A dermoscopy image of a single skin lesion:
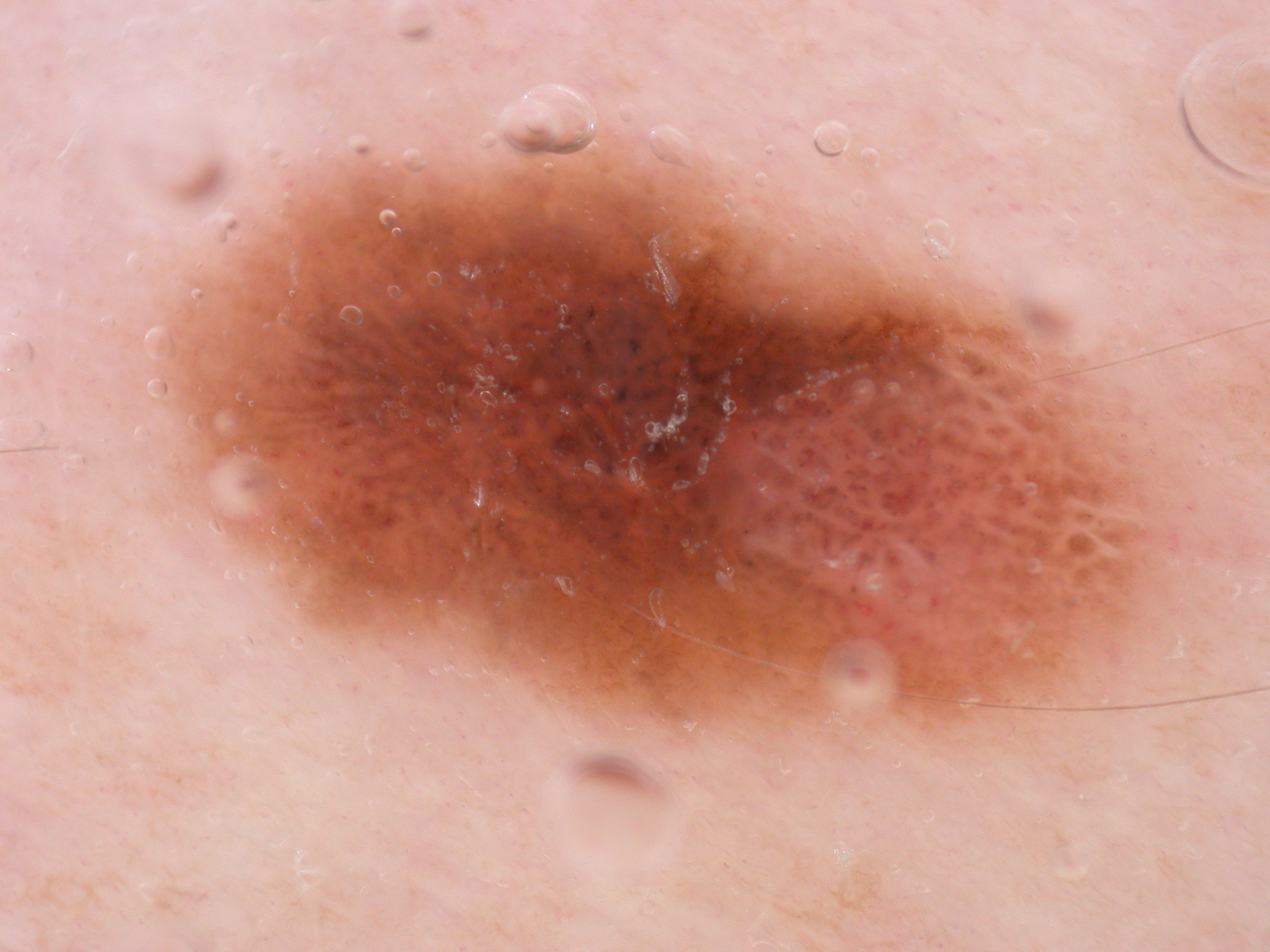dermoscopic_features:
  present:
    - negative network
    - globules
    - pigment network
  absent:
    - streaks
    - milia-like cysts
lesion_location:
  bbox_xyxy:
    - 156
    - 152
    - 1185
    - 757
lesion_extent:
  approx_field_fraction_pct: 38
diagnosis:
  name: melanocytic nevus
  malignancy: benign
  lineage: melanocytic
  provenance: clinical